A skin lesion imaged with a dermatoscope.
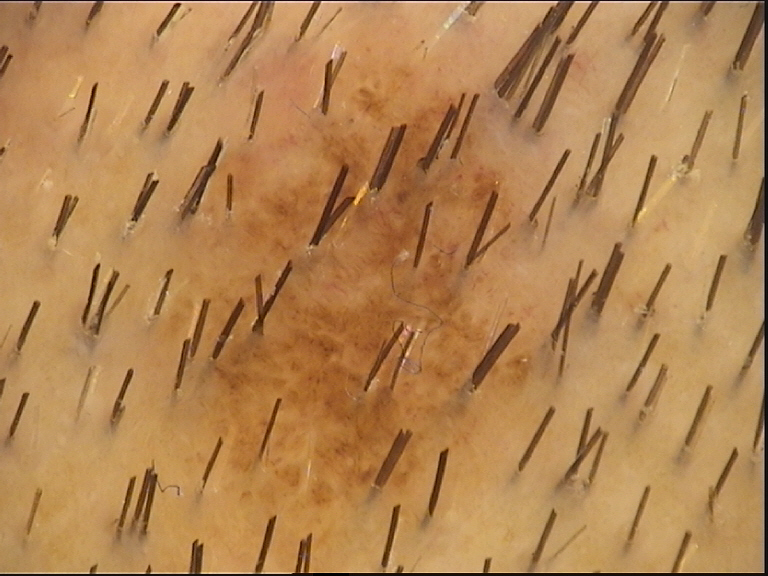Classified as a dysplastic junctional nevus.